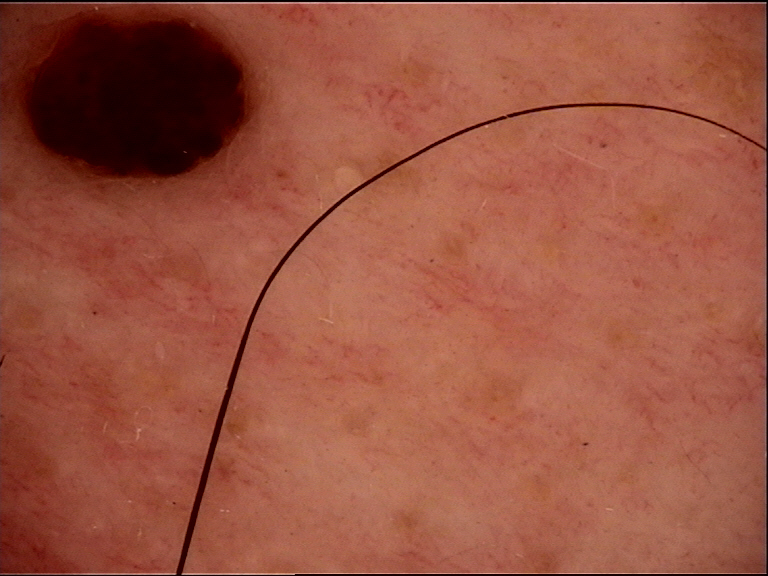Summary: This is a banal lesion. Conclusion: The diagnosis was a dermal nevus.